A dermoscopic close-up of a skin lesion: 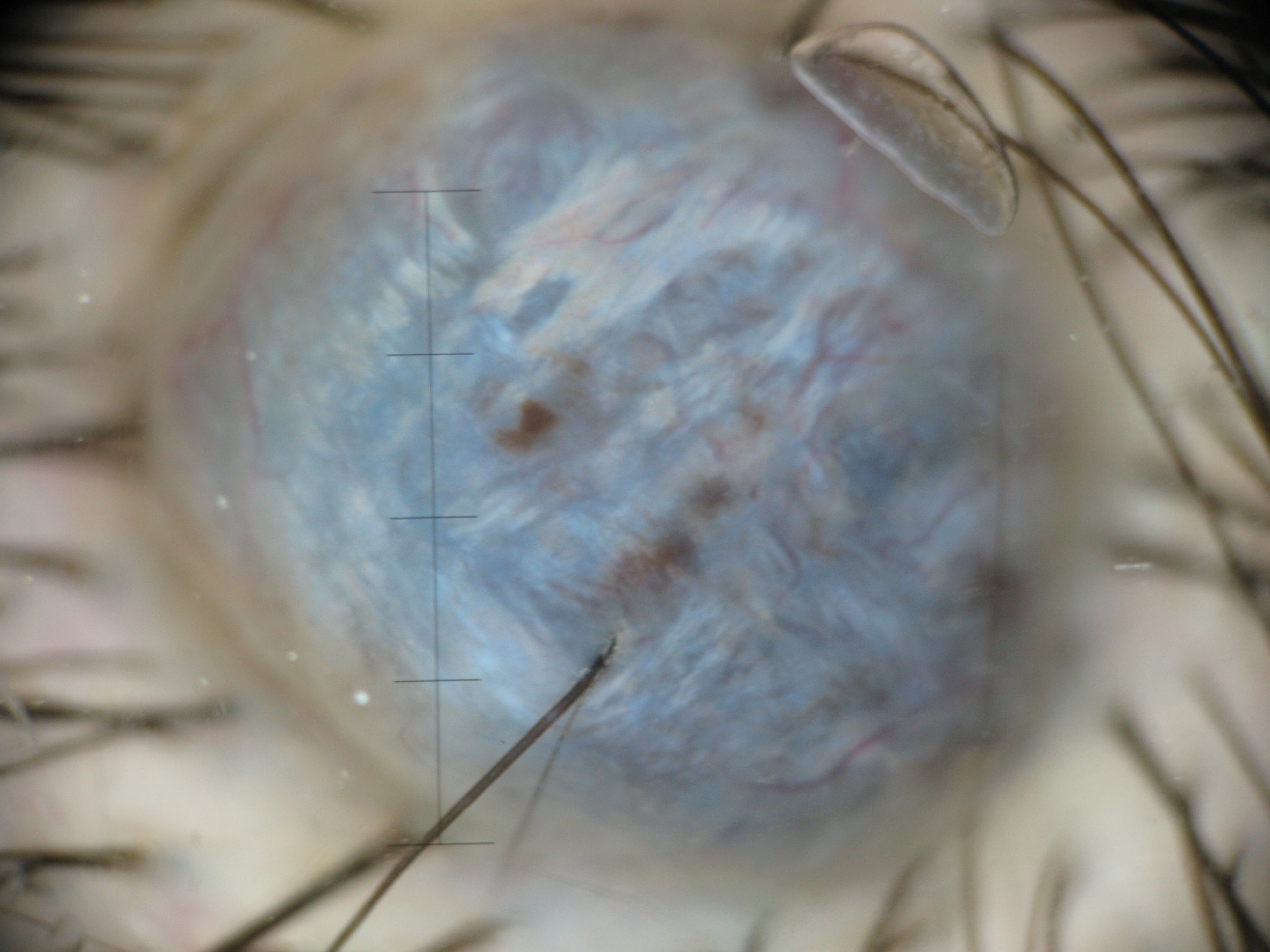Labeled as a banal lesion — a blue nevus.